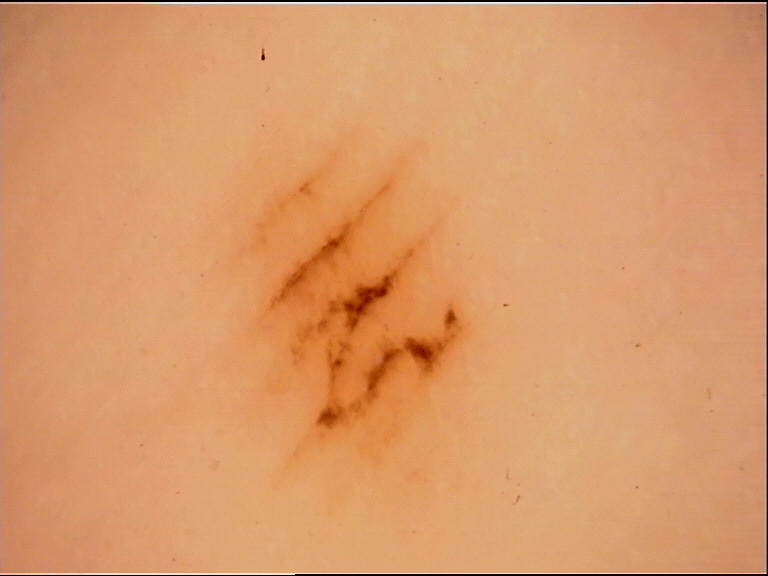image type: dermoscopy | subtype: banal | class: acral junctional nevus (expert consensus).